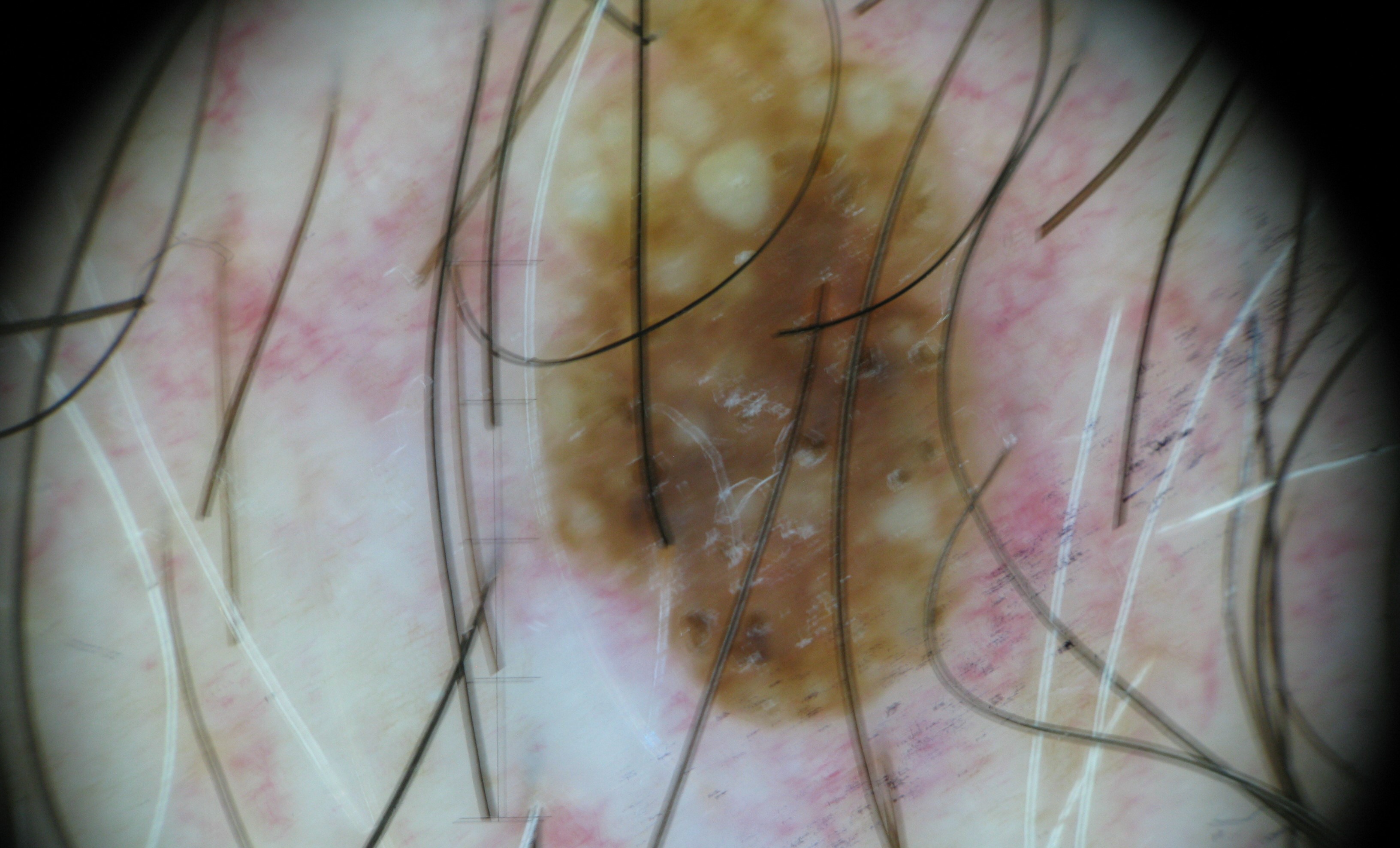A skin lesion imaged with a dermatoscope.
The diagnostic label was a keratinocytic, benign lesion — a seborrheic keratosis.